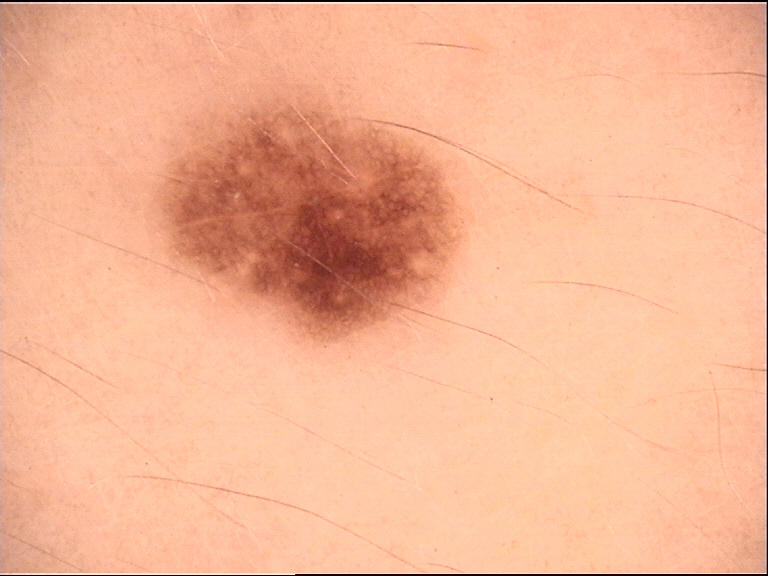A dermoscopy image of a single skin lesion. Consistent with a benign lesion — a dysplastic junctional nevus.